The chart records prior malignancy (patient or family) and prior skin cancer (patient or family). A female subject 51 years of age. The patient was assessed as Fitzpatrick III. A smartphone photograph of a skin lesion.
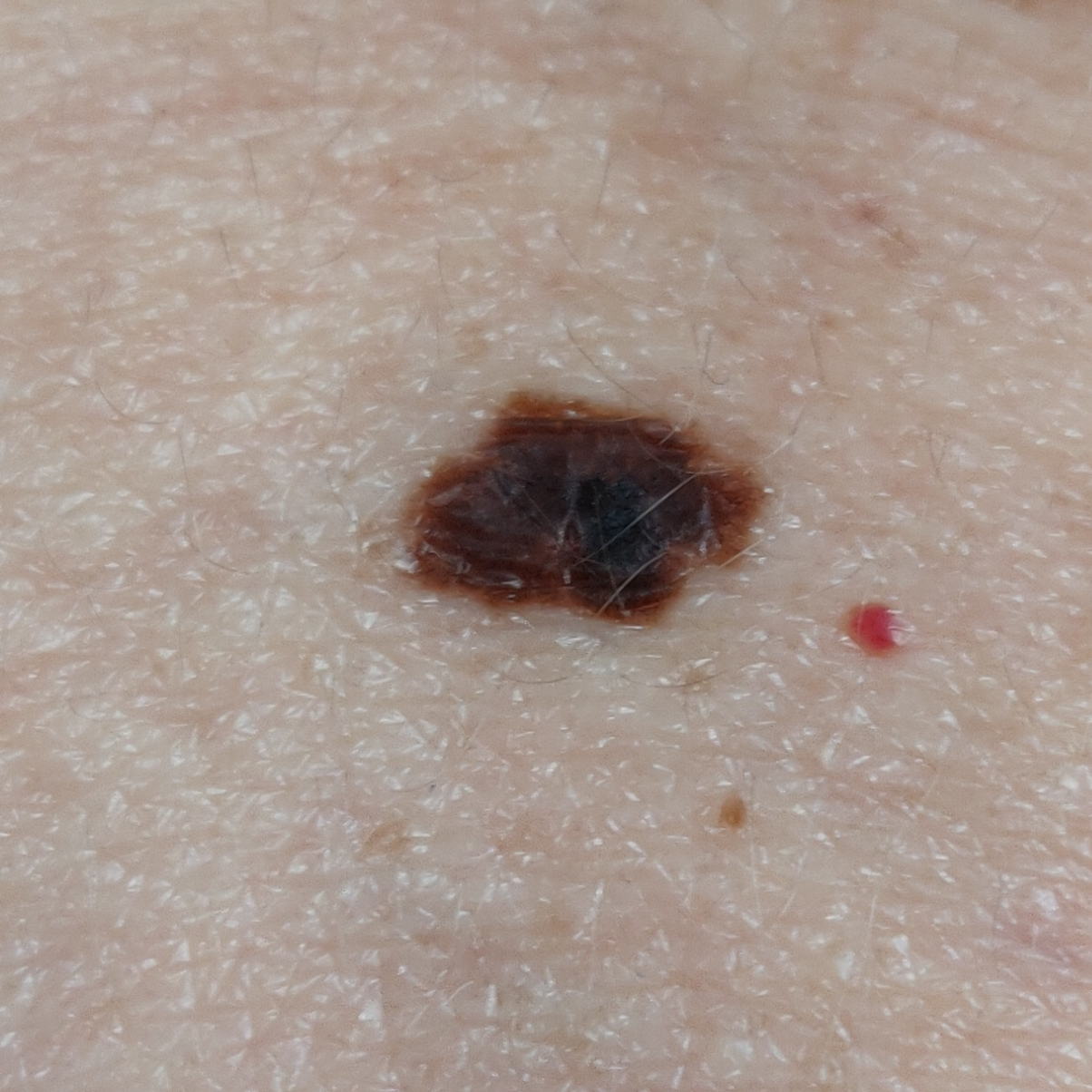The lesion was found on the back.
The lesion is roughly 6 by 4 mm.
By the patient's account, the lesion has changed and has grown.
Biopsy-confirmed as a nevus.